A skin lesion imaged with a dermatoscope.
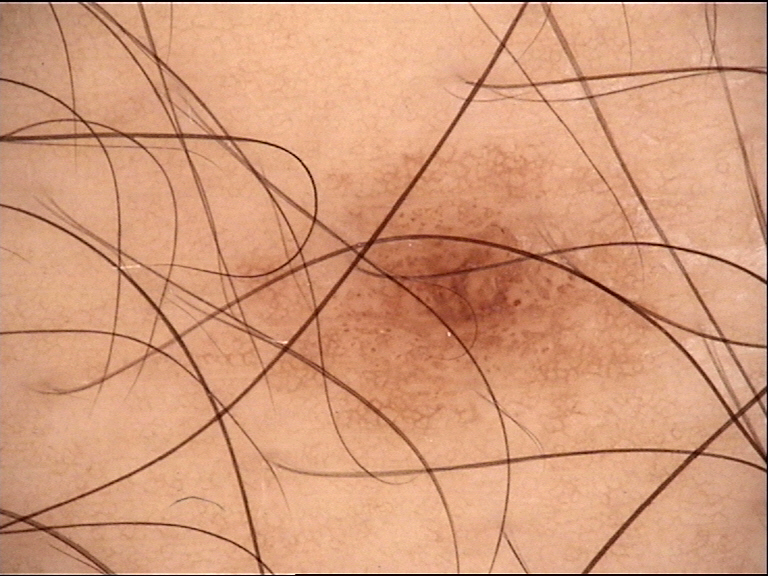diagnosis = junctional nevus (expert consensus).